A dermoscopic image of a skin lesion: 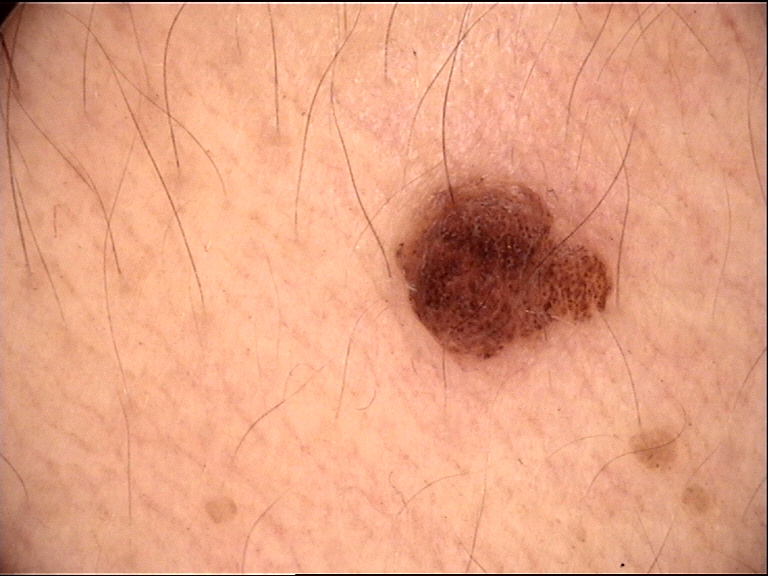Consistent with a banal lesion — a compound nevus.